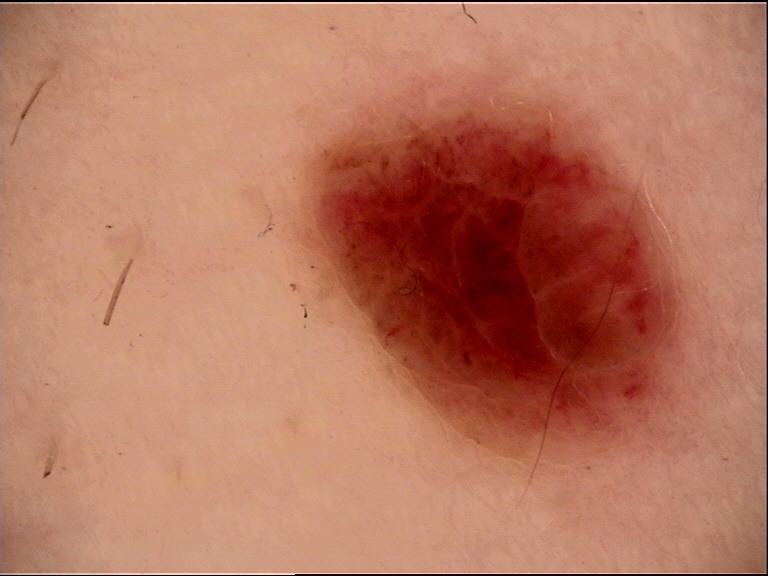| field | value |
|---|---|
| diagnostic label | compound nevus (expert consensus) |